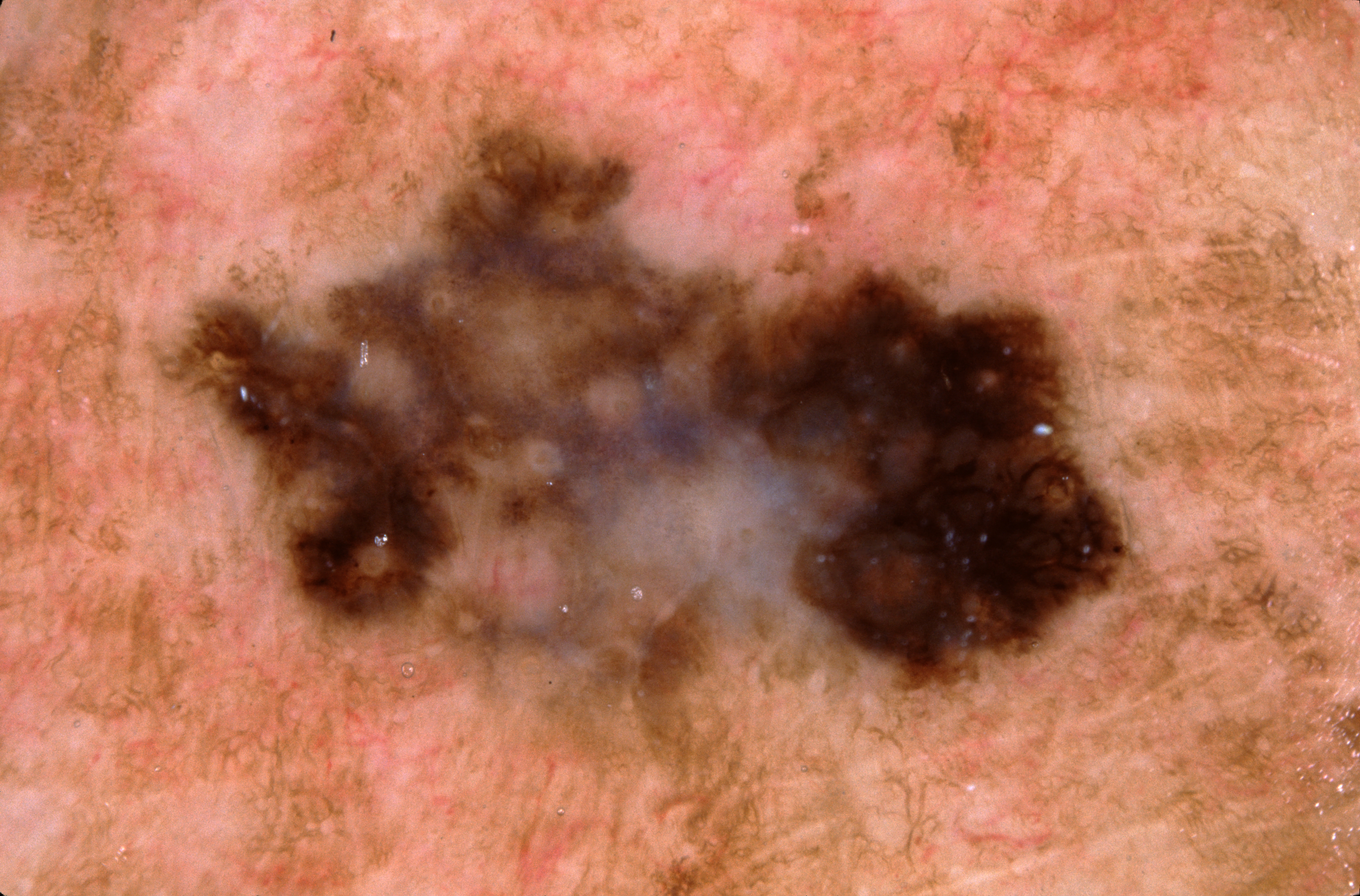Summary: A dermoscopic image of a skin lesion. A male subject, aged 63-67. A mid-sized lesion within the field. The visible lesion spans x1=191, y1=126, x2=1126, y2=693. Dermoscopic assessment notes pigment network; no milia-like cysts, negative network, or streaks. Diagnosis: Histopathology confirmed a melanoma, a skin cancer.